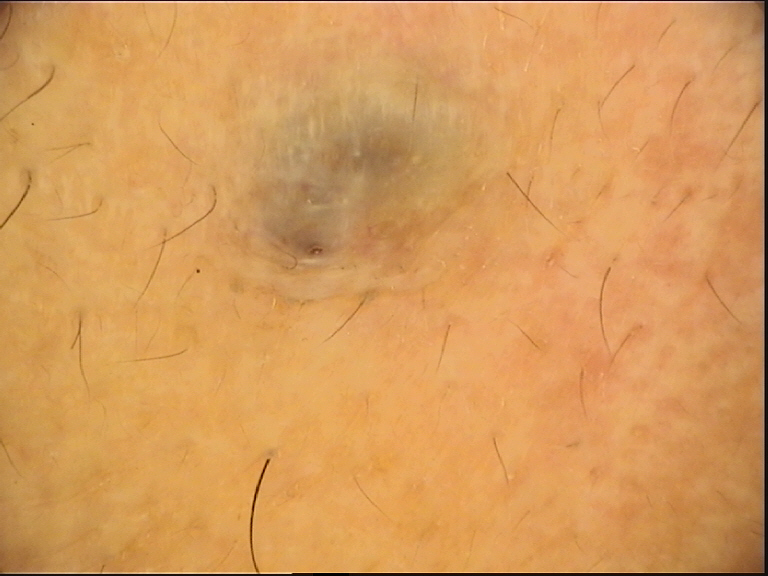Case:
A dermoscopy image of a single skin lesion.
Conclusion:
The diagnostic label was a dermal lesion — a blue nevus.